A dermoscopic image of a skin lesion: 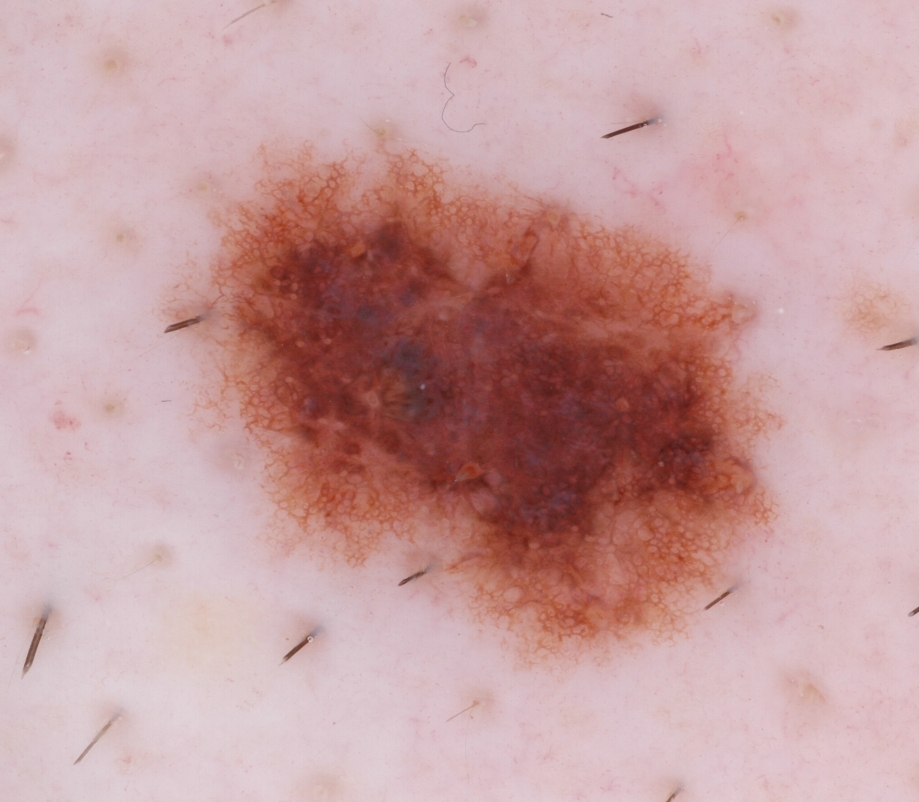Notes:
- size — ~31% of the field
- lesion location — x1=161, y1=119, x2=782, y2=664
- dermoscopic findings — globules and pigment network; absent: milia-like cysts, streaks, and negative network
- assessment — a melanocytic nevus, a benign skin lesion